The patient is female. The lesion involves the back of the hand. The photo was captured at a distance: 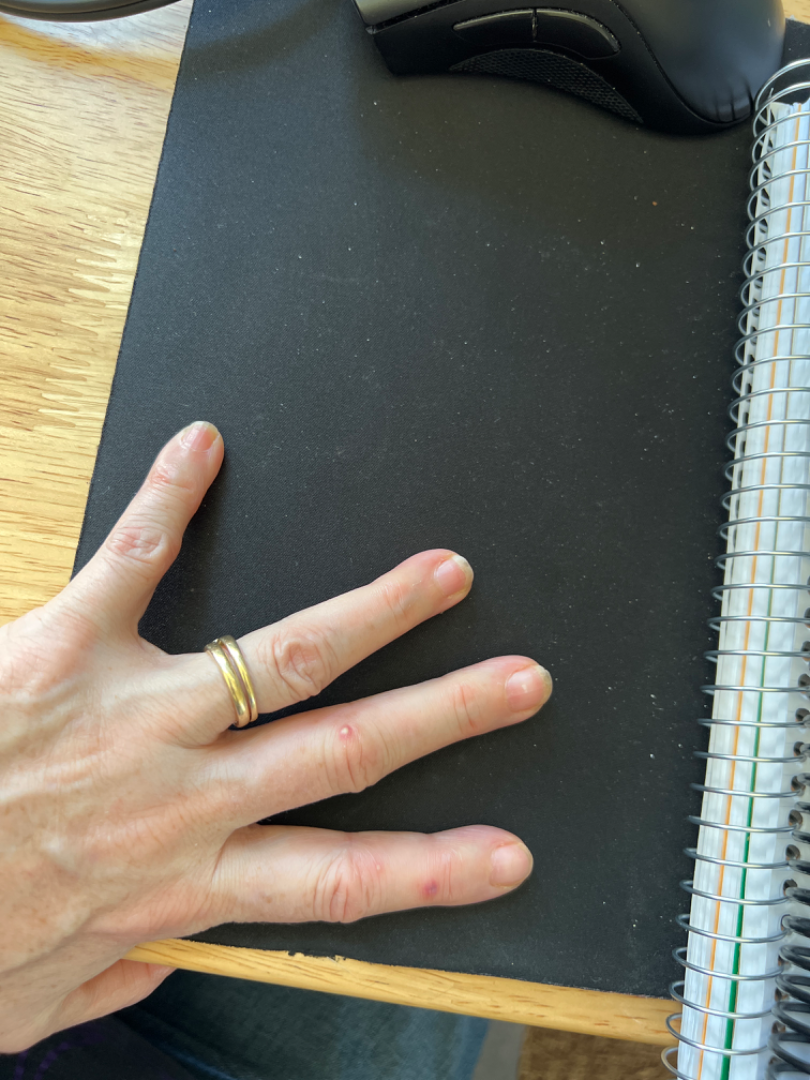History: Texture is reported as fluid-filled. Skin tone: non-clinician graders estimated a MST of 2. The patient considered this a rash. Reported duration is about one day. Impression: A single dermatologist reviewed the case: Impetigo, Chilblain and Leukocytoclastic Vasculitis were considered with similar weight.